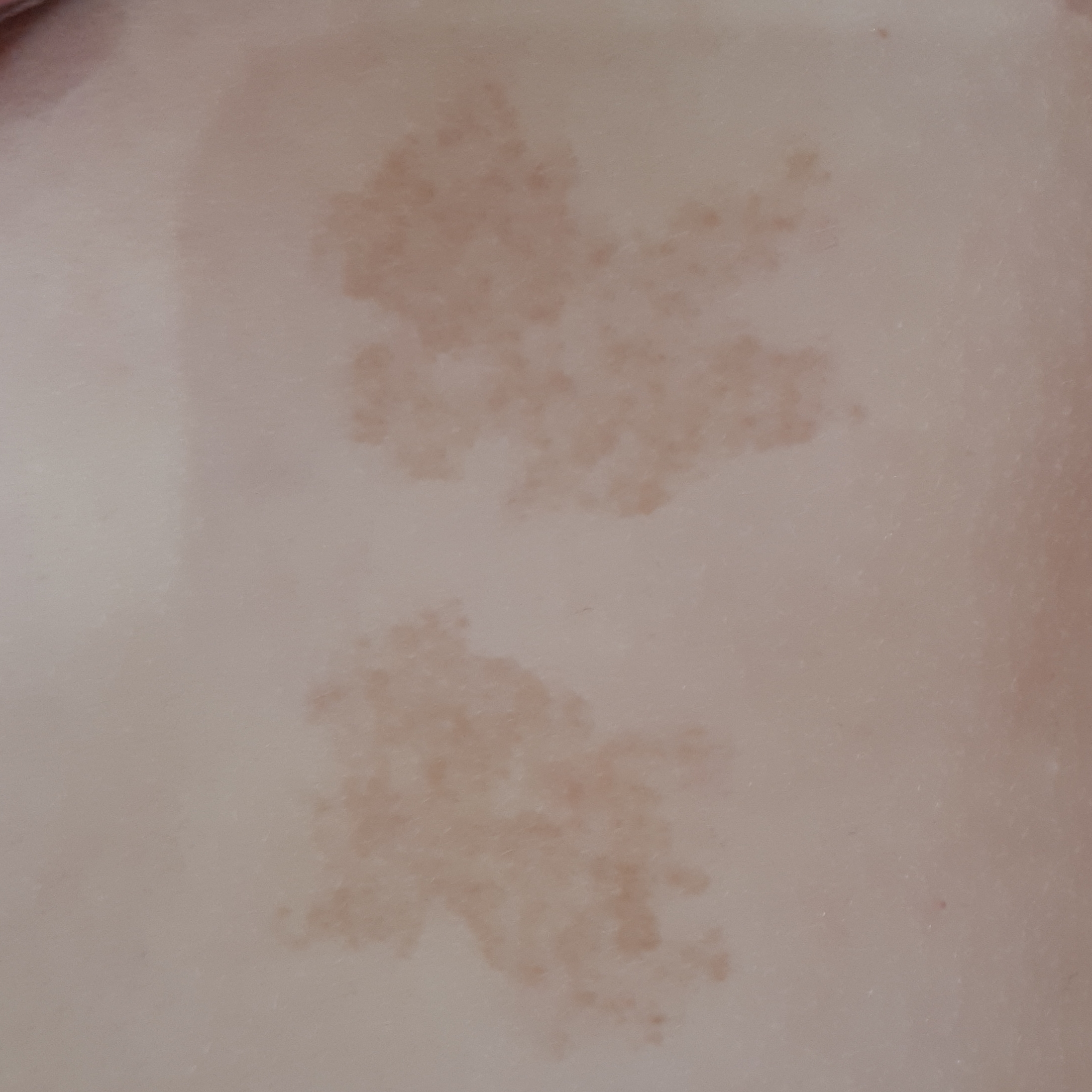<lesion>
  <diagnosis>
    <name>nevus</name>
    <code>NEV</code>
    <malignancy>benign</malignancy>
    <confirmation>clinical consensus</confirmation>
  </diagnosis>
</lesion>